A dermoscopic photograph of a skin lesion.
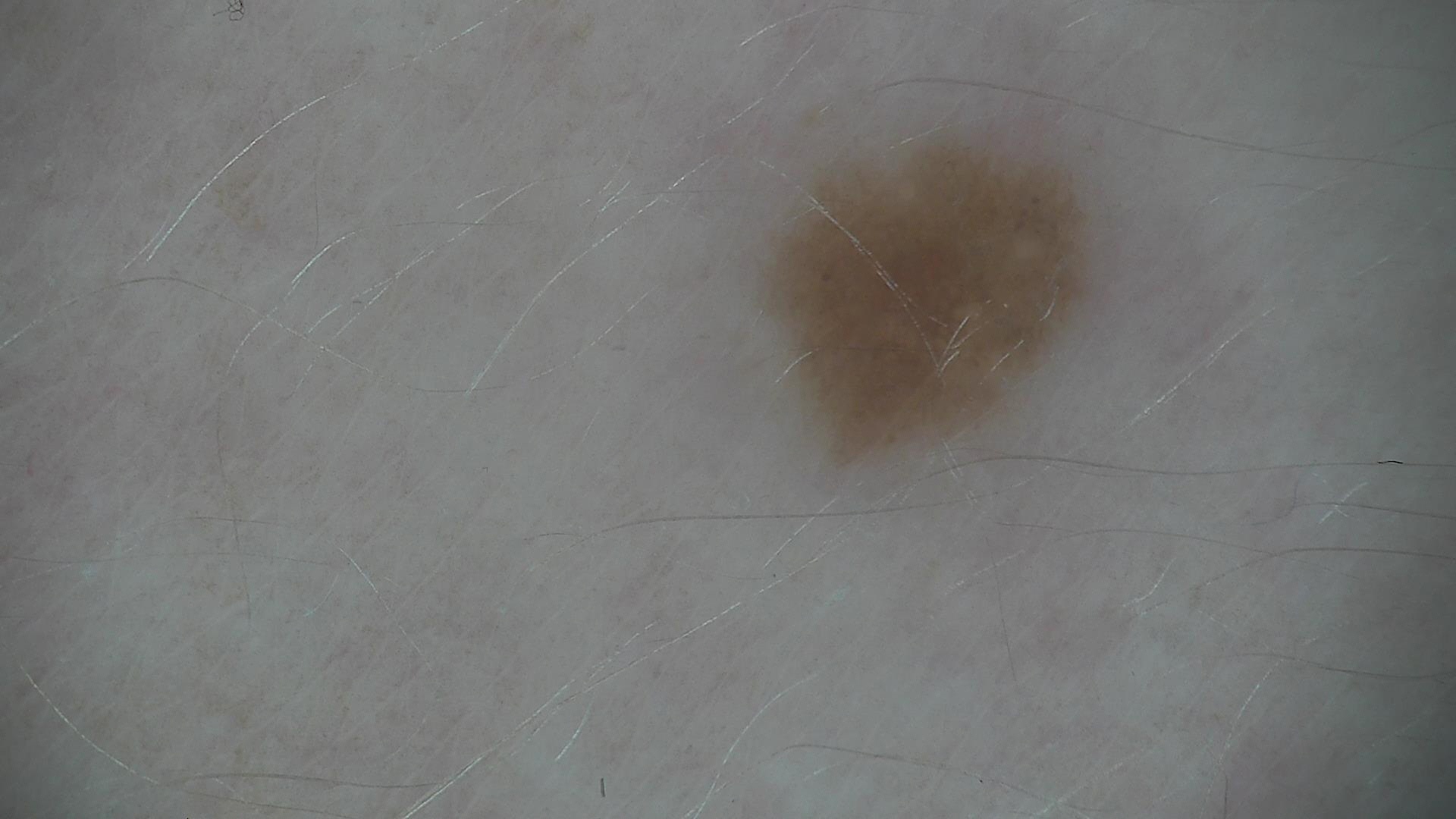Diagnosed as a dysplastic junctional nevus.